A dermoscopic view of a skin lesion:
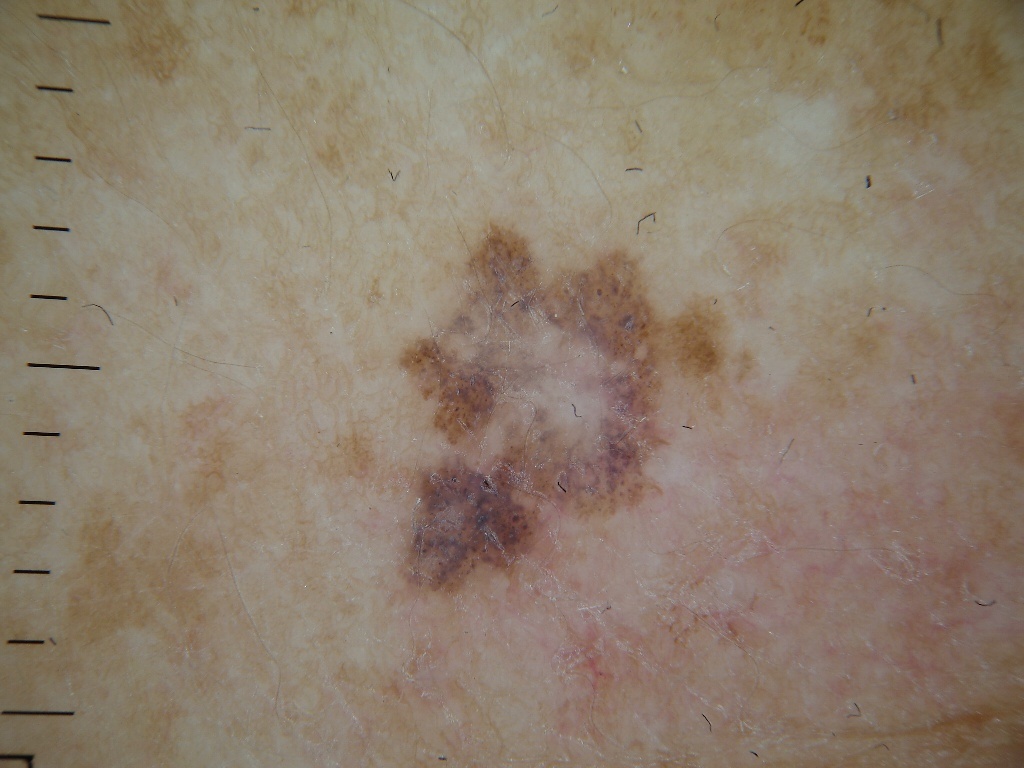Image and clinical context: On dermoscopy, the lesion shows no globules or streaks. With coordinates (x1, y1, x2, y2), the lesion is located at <box>398, 227, 722, 603</box>. Conclusion: The clinical diagnosis was a benign skin lesion.